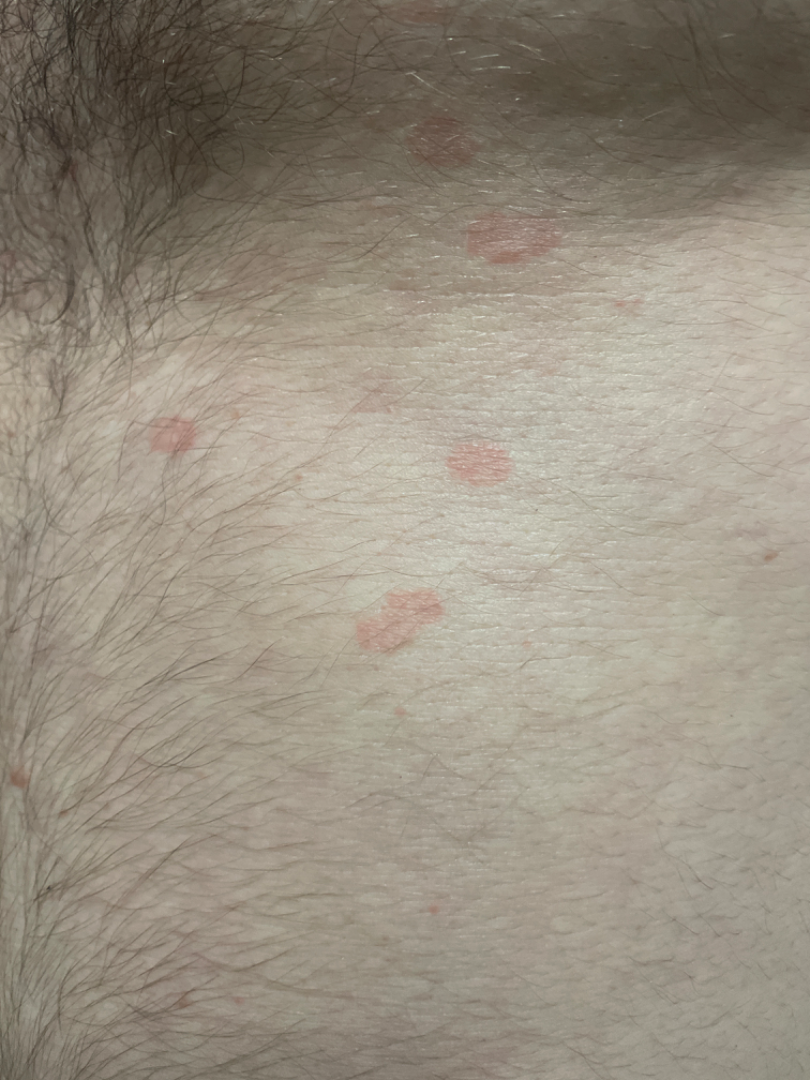Findings:
On photographic review: the leading consideration is Eczema; possibly Pityriasis rosea; lower on the differential is Psoriasis.